A clinical photo of a skin lesion taken with a smartphone. History notes prior malignancy (patient or family). The patient is Fitzpatrick skin type II. A male subject 71 years of age — 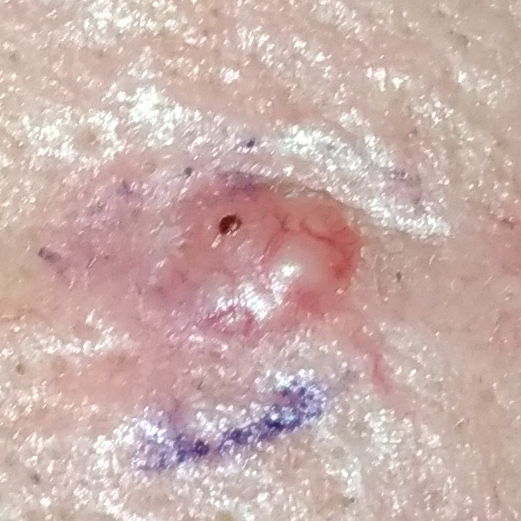Findings:
Measuring about 6 × 5 mm. By the patient's account, the lesion has grown, itches, has bled, and is elevated, but has not changed.
Diagnosis:
Histopathologically confirmed as a basal cell carcinoma.